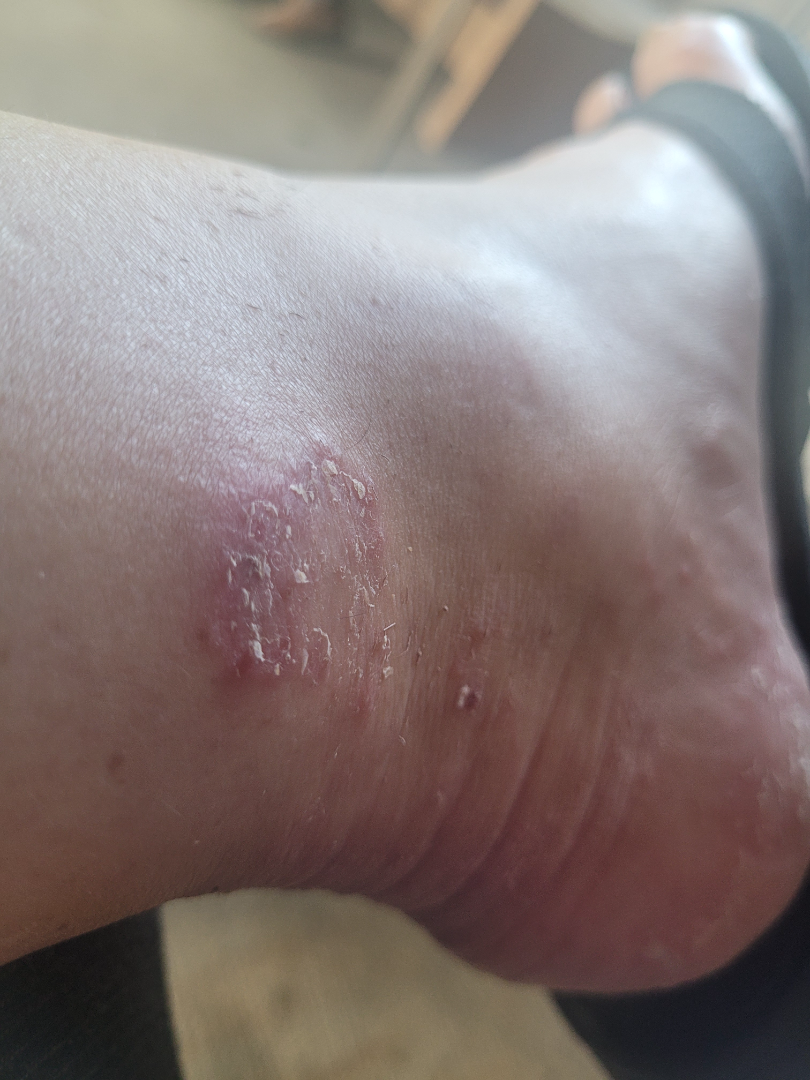The patient considered this a rash. The photograph was taken at an angle. The lesion is described as rough or flaky and raised or bumpy. The lesion is associated with enlargement and itching. No constitutional symptoms were reported. The affected area is the leg and sole of the foot. On remote dermatologist review: the leading consideration is Tinea.